A dermoscopic image of a skin lesion: 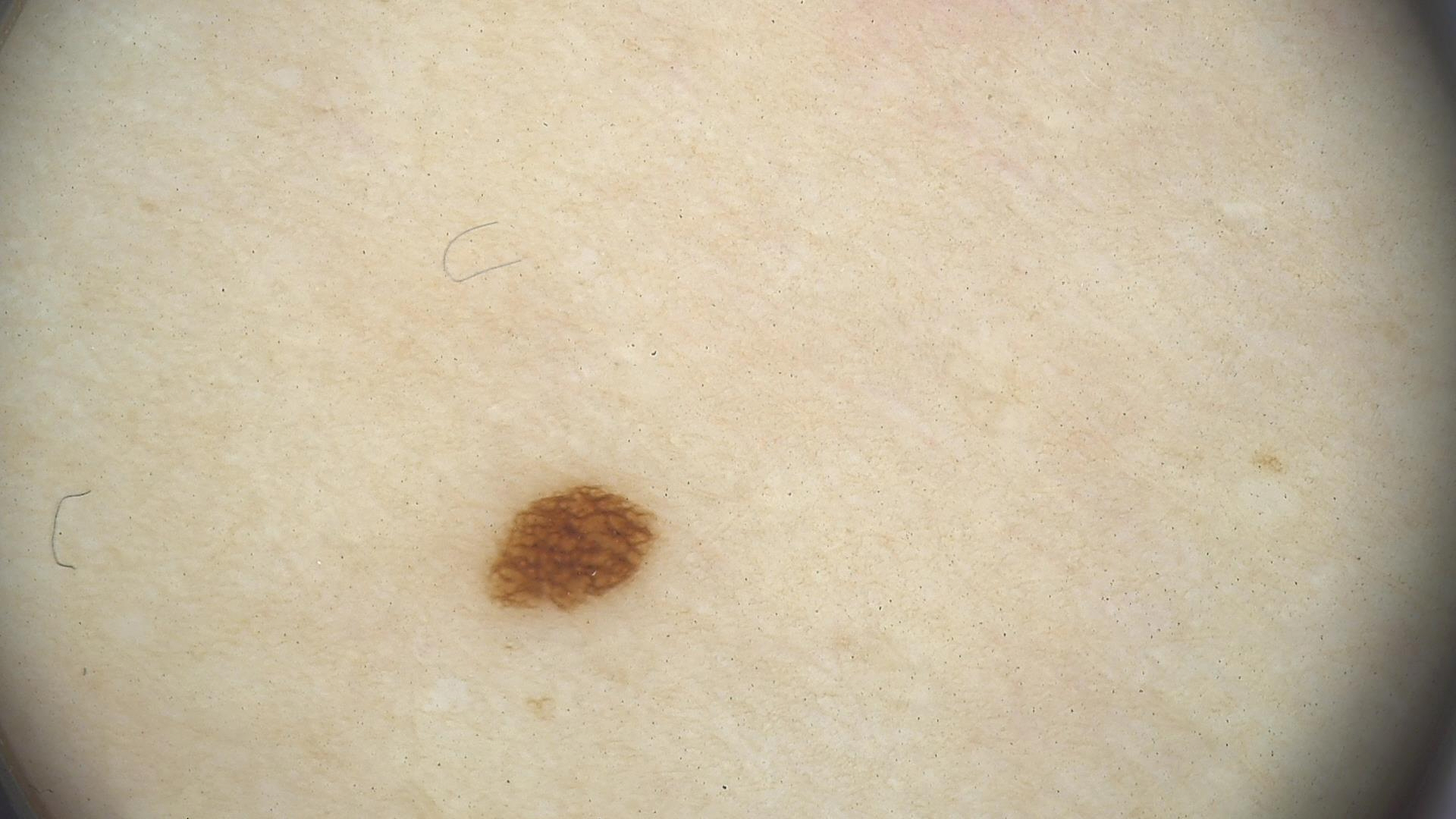{
  "diagnosis": {
    "name": "junctional nevus",
    "code": "jb",
    "malignancy": "benign",
    "super_class": "melanocytic",
    "confirmation": "expert consensus"
  }
}